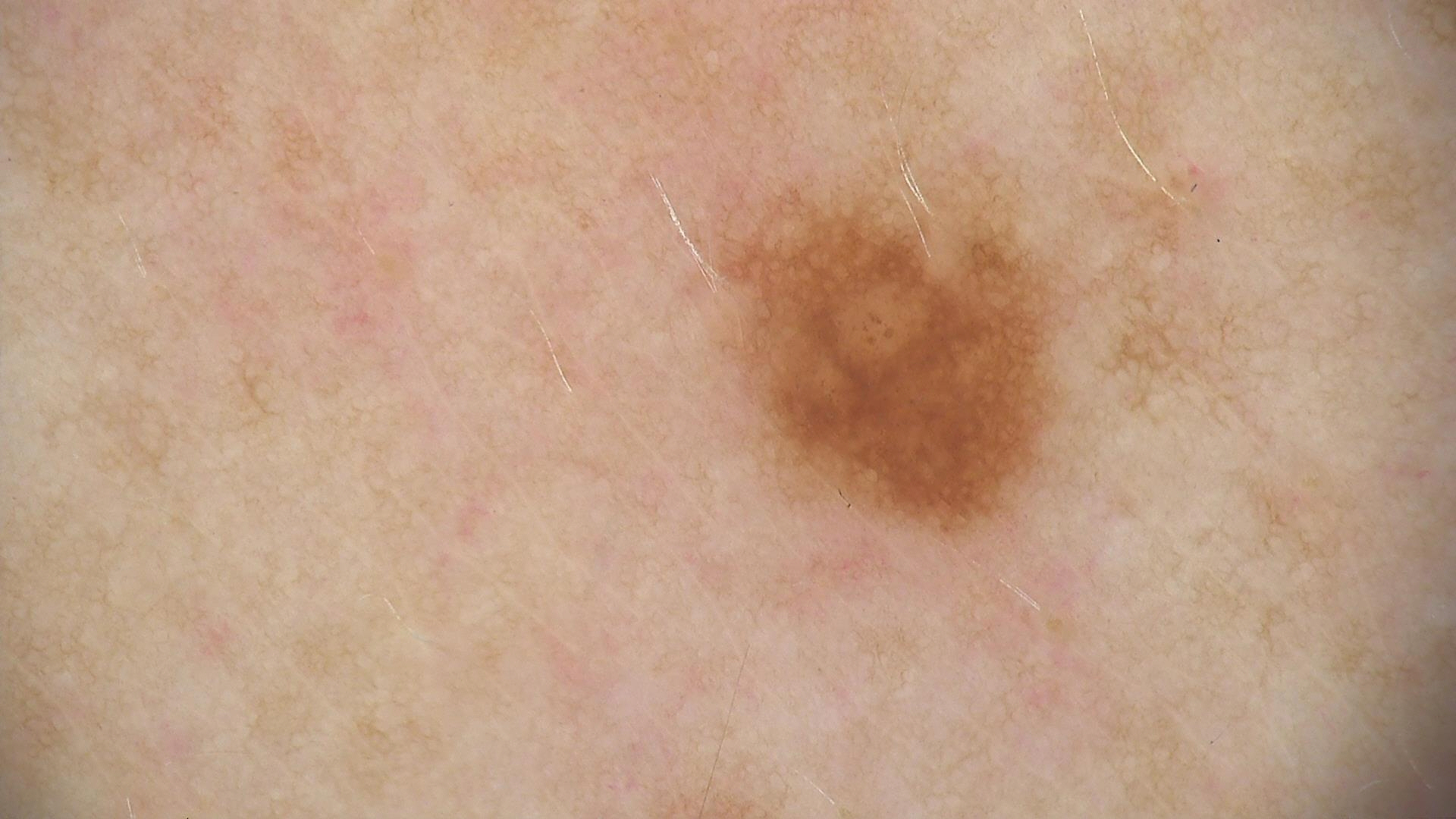Labeled as a dysplastic junctional nevus.